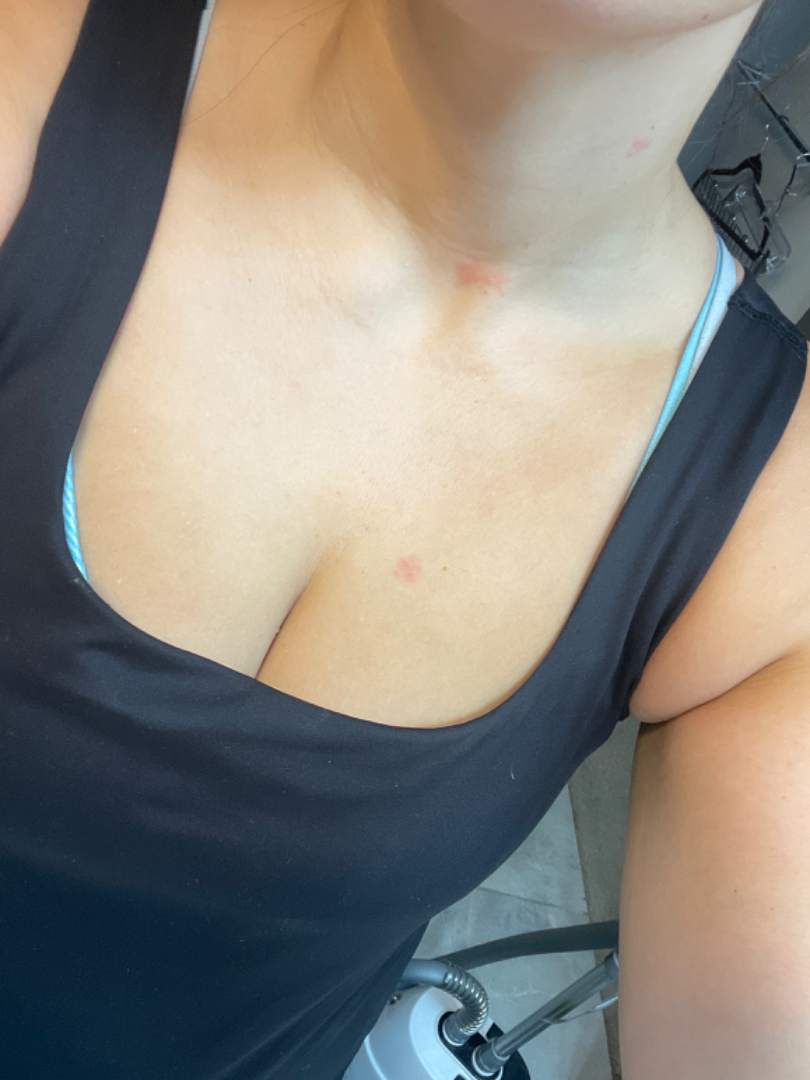Notes:
- framing — at an angle
- reported symptoms — pain and burning
- affected area — head or neck
- skin tone — Fitzpatrick III; lay reviewers estimated Monk Skin Tone 4 (US pool) or 3 (India pool)
- patient describes the issue as — a rash
- contributor — female, age 30–39
- texture — raised or bumpy
- duration — about one day
- dermatologist impression — three dermatologists each reviewed the case: most consistent with Eczema; with consideration of Allergic Contact Dermatitis; also on the differential is Tinea; less likely is Contact dermatitis